A dermoscopy image of a single skin lesion.
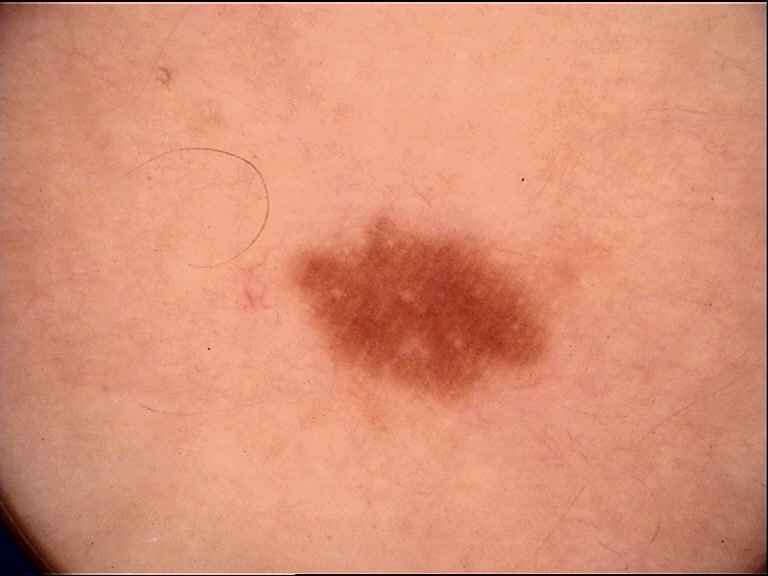Diagnosed as a dysplastic junctional nevus.